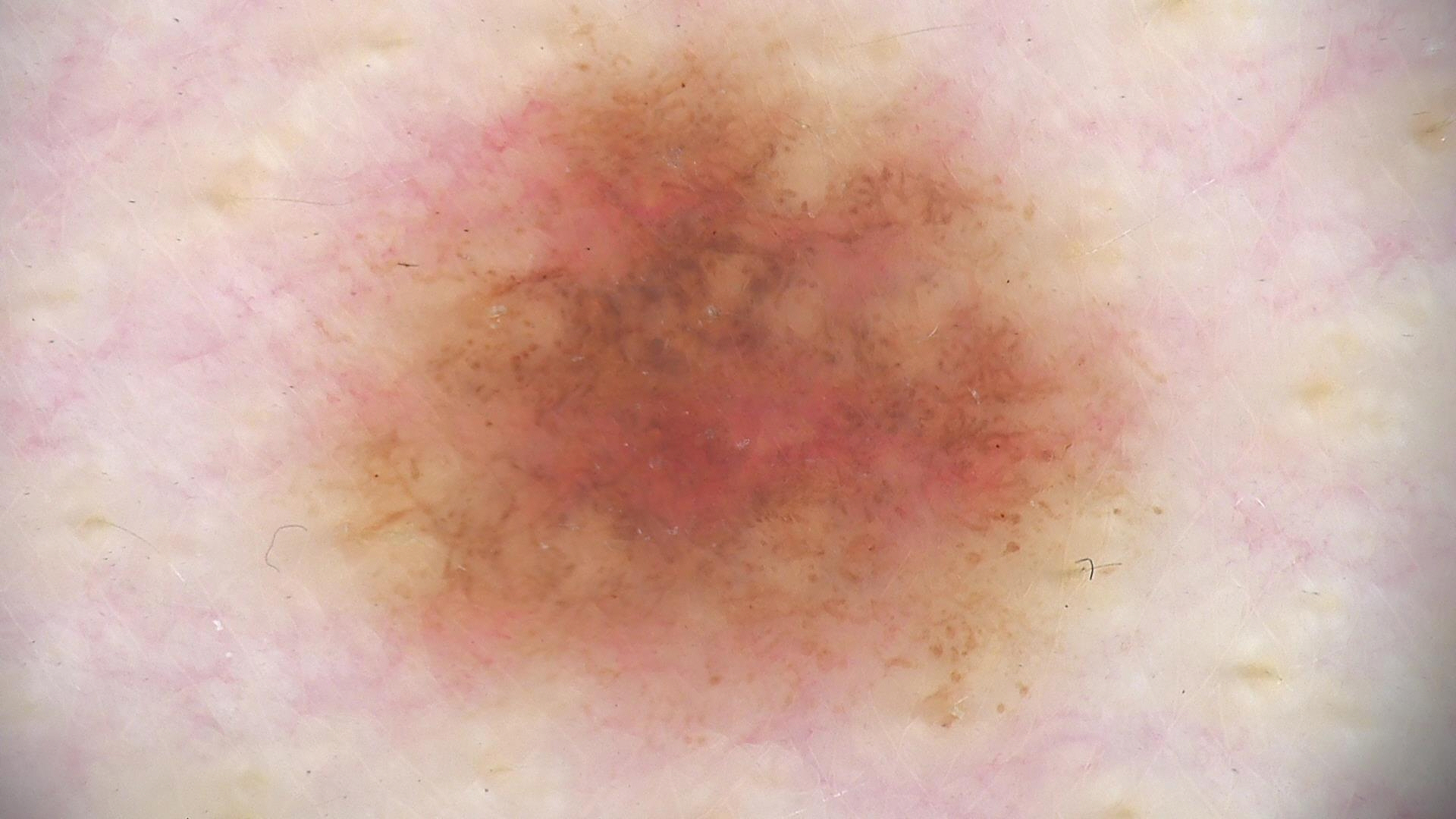Q: What kind of image is this?
A: dermatoscopy
Q: What is this lesion?
A: dysplastic junctional nevus (expert consensus)